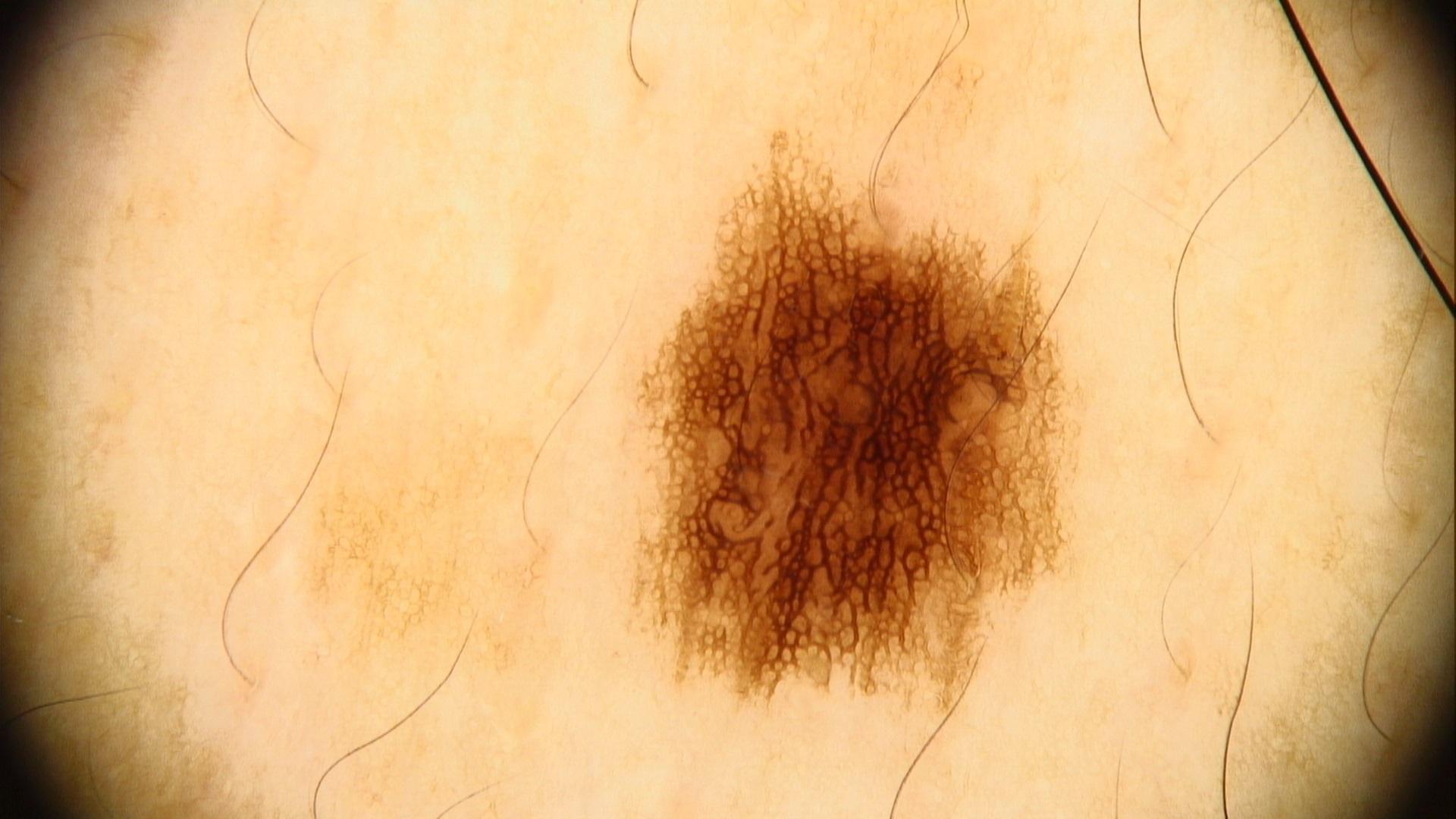{
  "image": "dermoscopic image",
  "diagnosis": {
    "name": "Nevus",
    "malignancy": "benign",
    "confirmation": "expert clinical impression",
    "lineage": "melanocytic"
  }
}